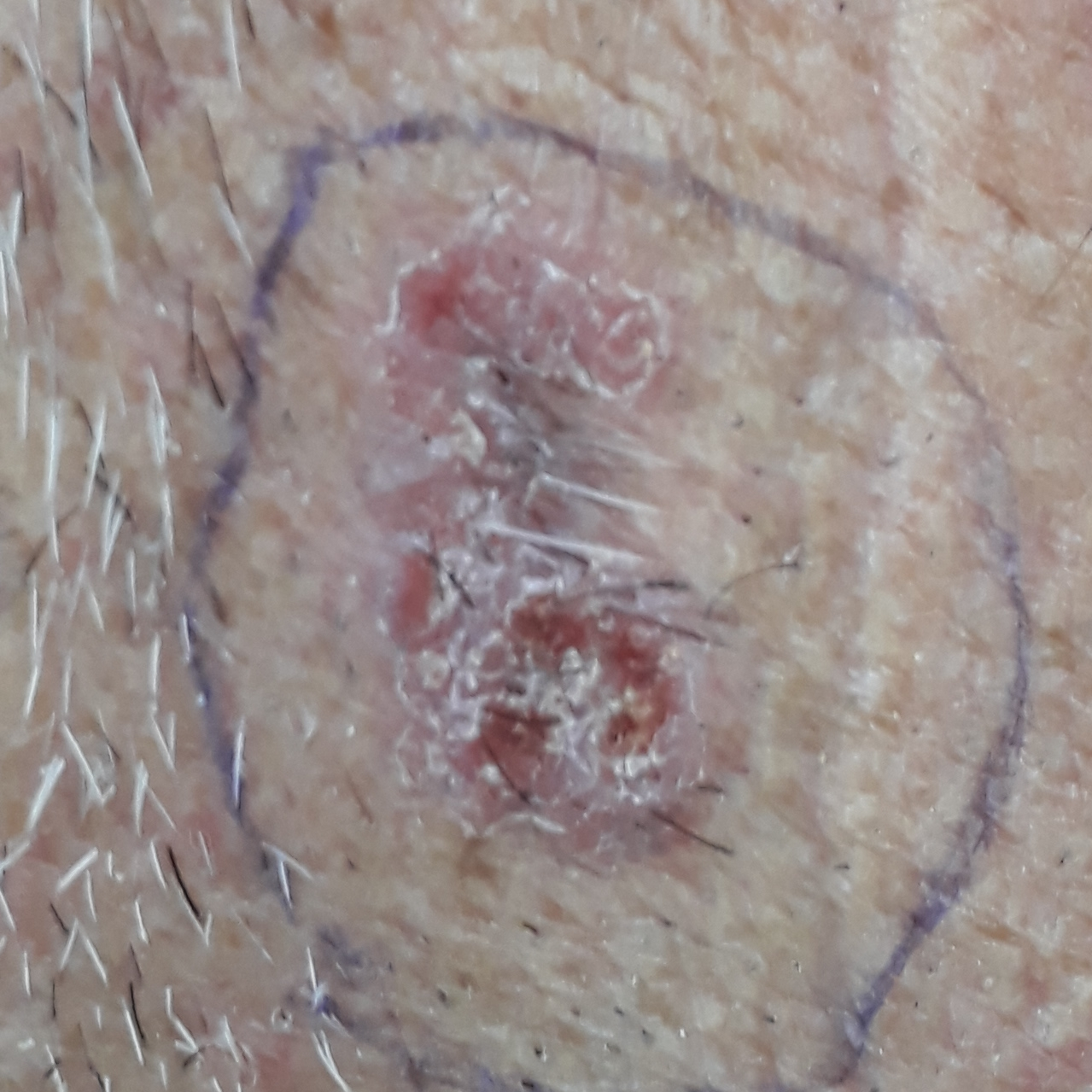Findings:
* imaging — smartphone clinical photo
* subject — male, age 64
* region — the neck
* lesion diameter — 20 × 10 mm
* symptoms — itching, bleeding, elevation, pain
* diagnosis — basal cell carcinoma (biopsy-proven)